Female subject, age 30–39; the affected area is the leg; reported lesion symptoms include itching; close-up view; the lesion is described as raised or bumpy; self-categorized by the patient as a rash; Fitzpatrick II; the condition has been present for one to four weeks.
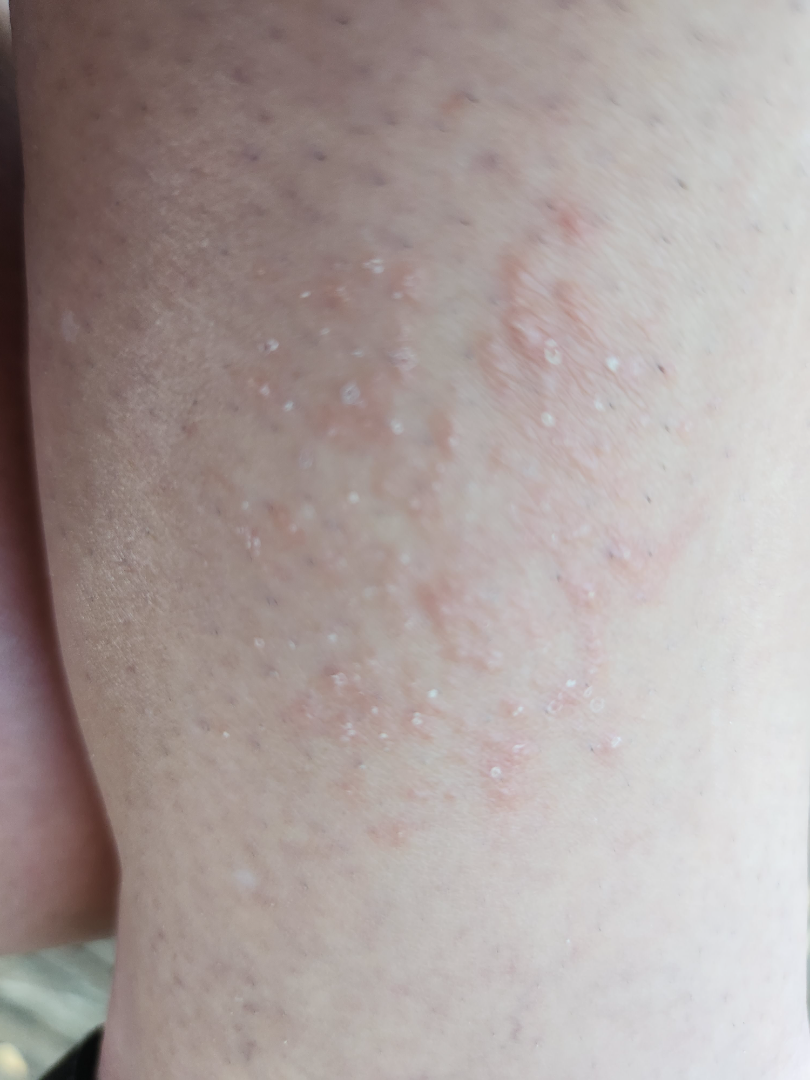Notes:
* differential · the impression was split between Keratosis pilaris and Lichen spinulosus; a remote consideration is Folliculitis